Fitzpatrick phototype II; a clinical photograph of a skin lesion: 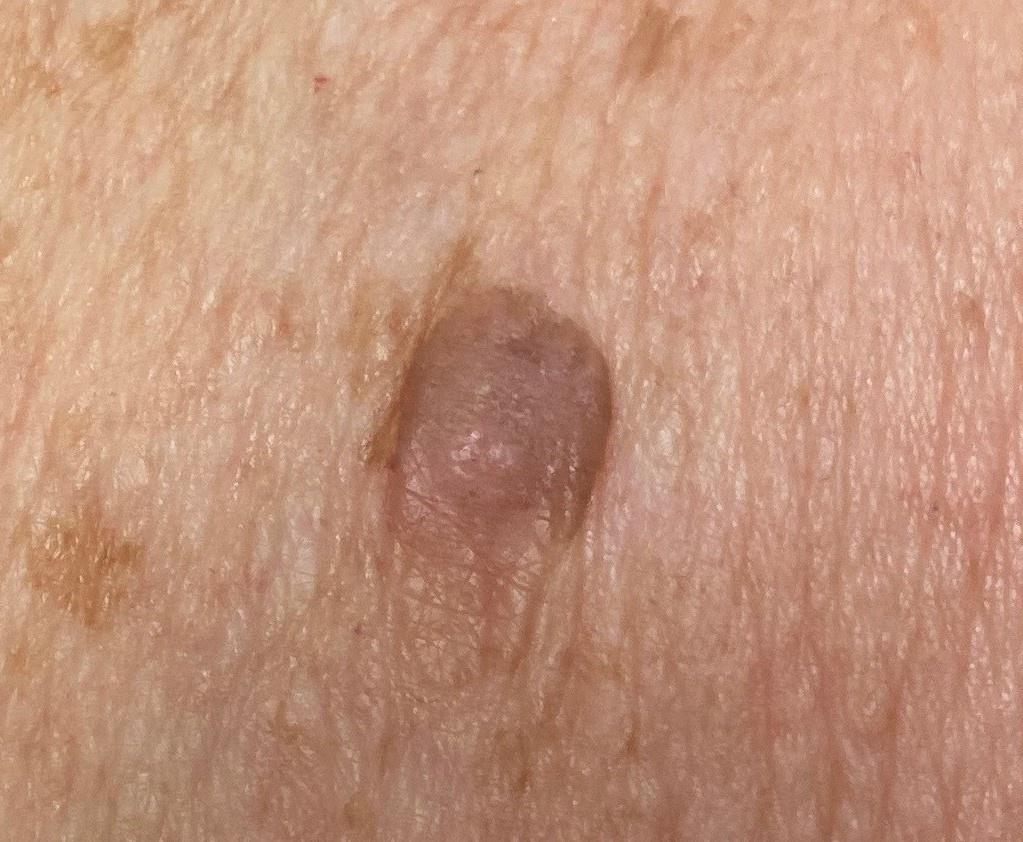Q: What is the anatomic site?
A: the anterior trunk
Q: What is the diagnosis?
A: Squamous cell carcinoma (biopsy-proven)